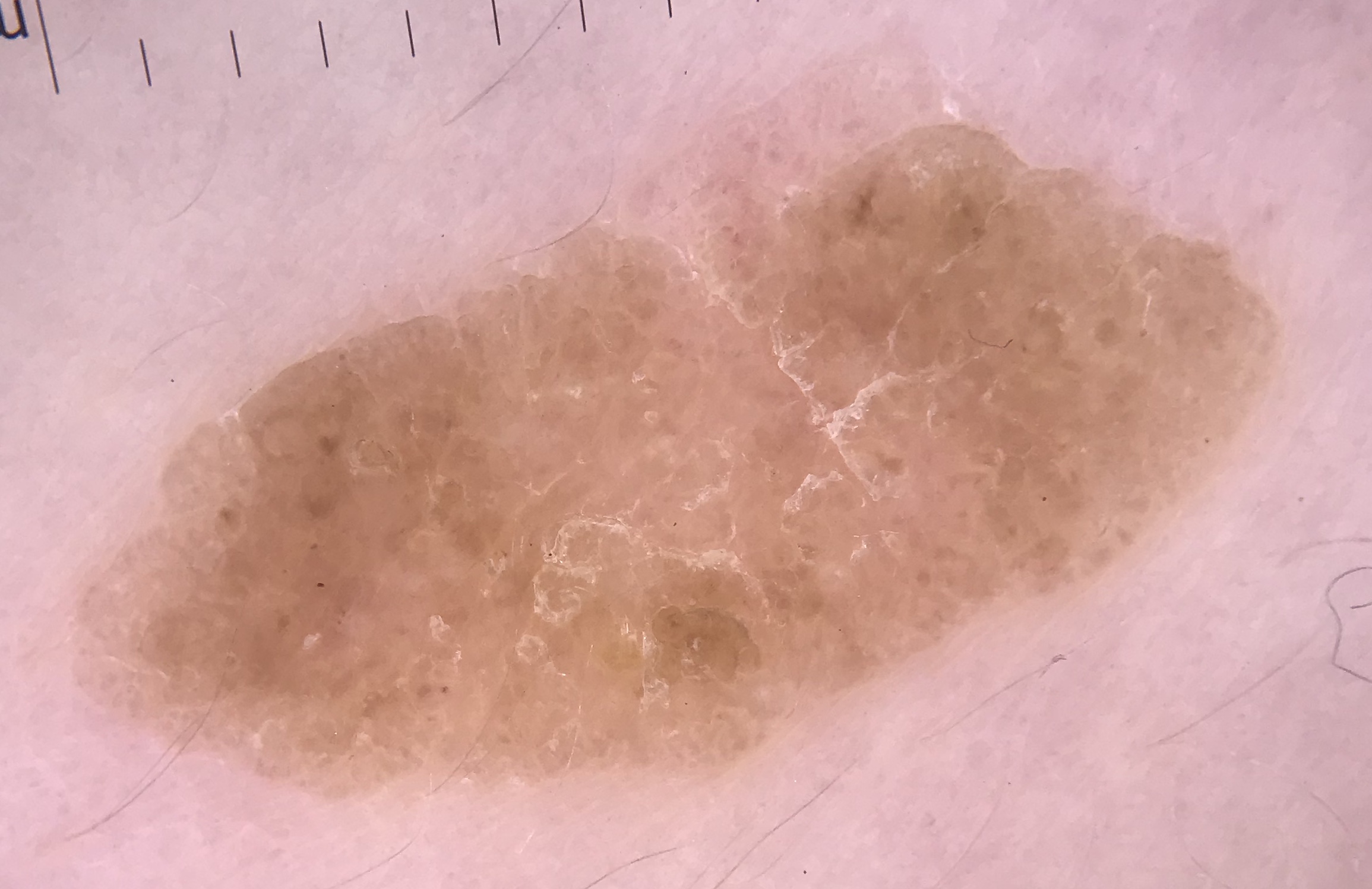diagnosis: seborrheic keratosis (expert consensus)